A close-up photograph, the lesion is described as flat, located on the arm and leg, self-categorized by the patient as a rash, reported duration is less than one week: 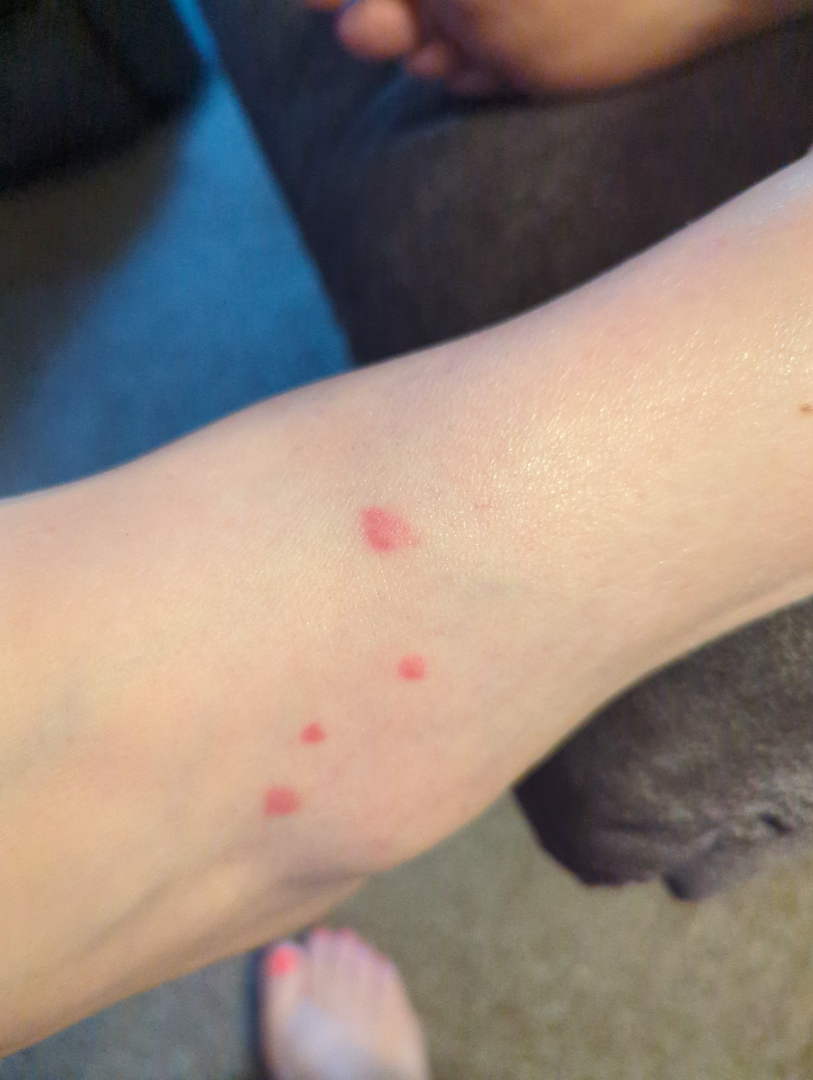Q: Could the case be diagnosed?
A: indeterminate from the photograph